This image was taken at a distance. The patient indicates itching. Self-categorized by the patient as a rash. The condition has been present for one to four weeks. Located on the leg and arm:
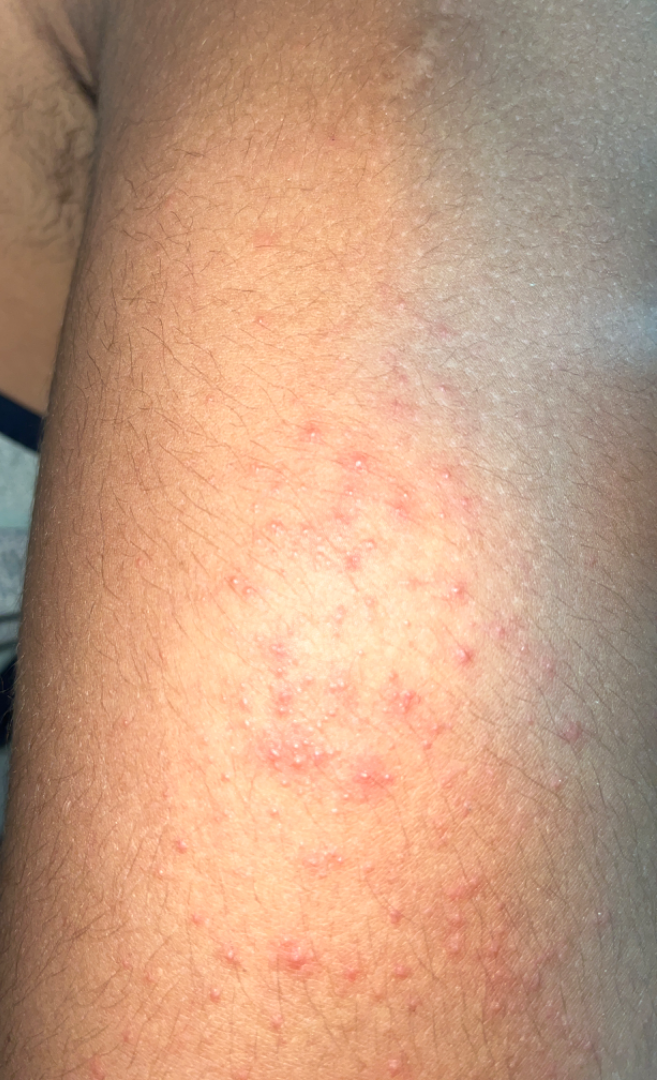Q: What was the assessment?
A: not assessable